The top or side of the foot is involved · present for less than one week · texture is reported as raised or bumpy · this image was taken at an angle · the patient described the issue as skin that appeared healthy to them: 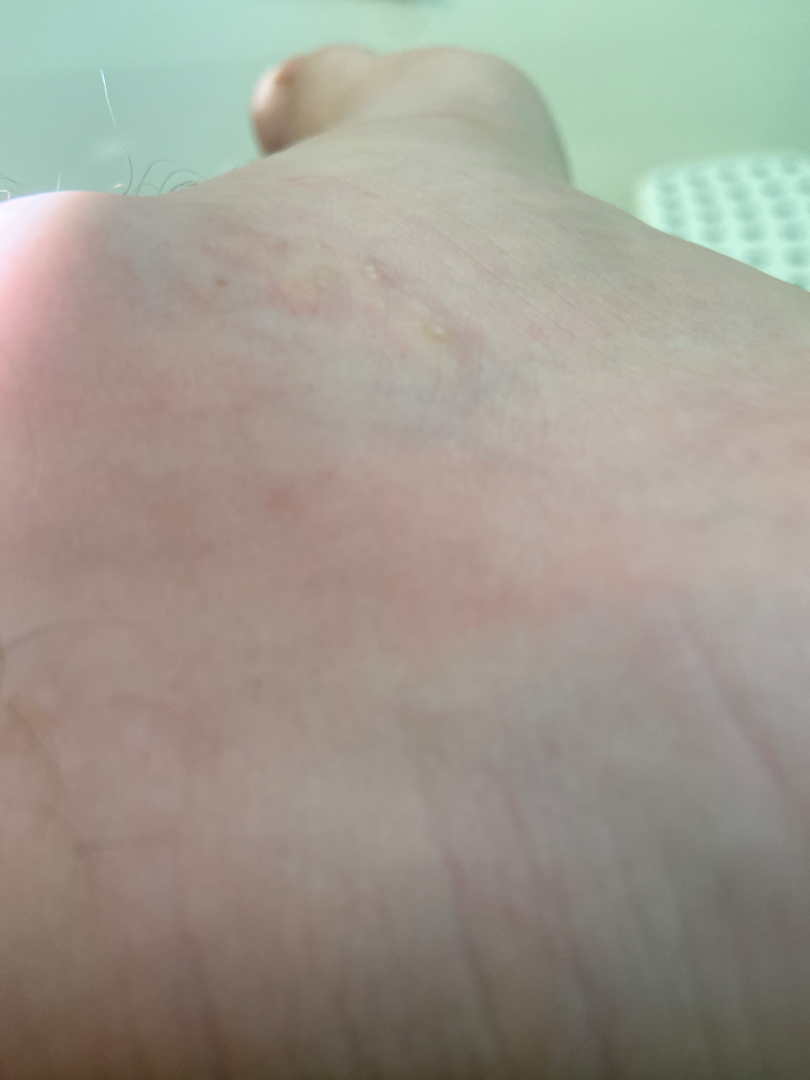{
  "assessment": "not assessable"
}